A close-up photograph · the lesion involves the top or side of the foot · the subject is 30–39, female — 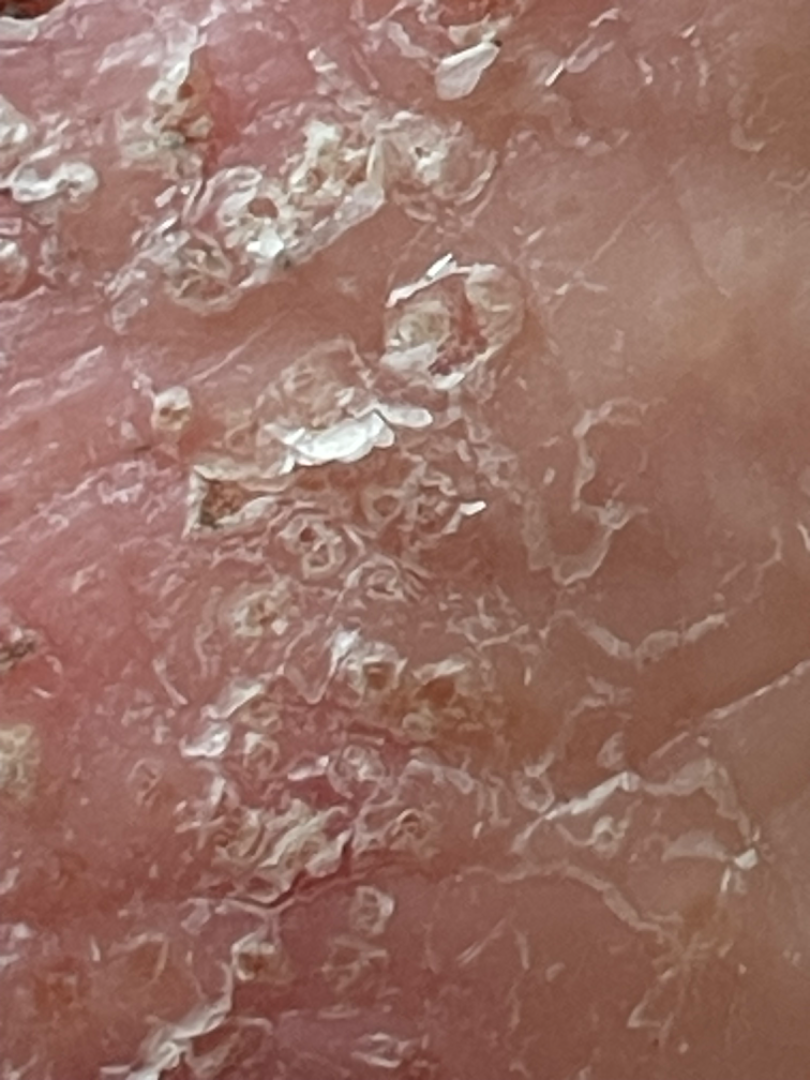The contributor notes the lesion is raised or bumpy, fluid-filled and rough or flaky. The lesion is associated with itching. Skin tone: Fitzpatrick phototype III. Reported duration is more than one year. On photographic review by a dermatologist, the leading impression is Tinea; also on the differential is Eczema.